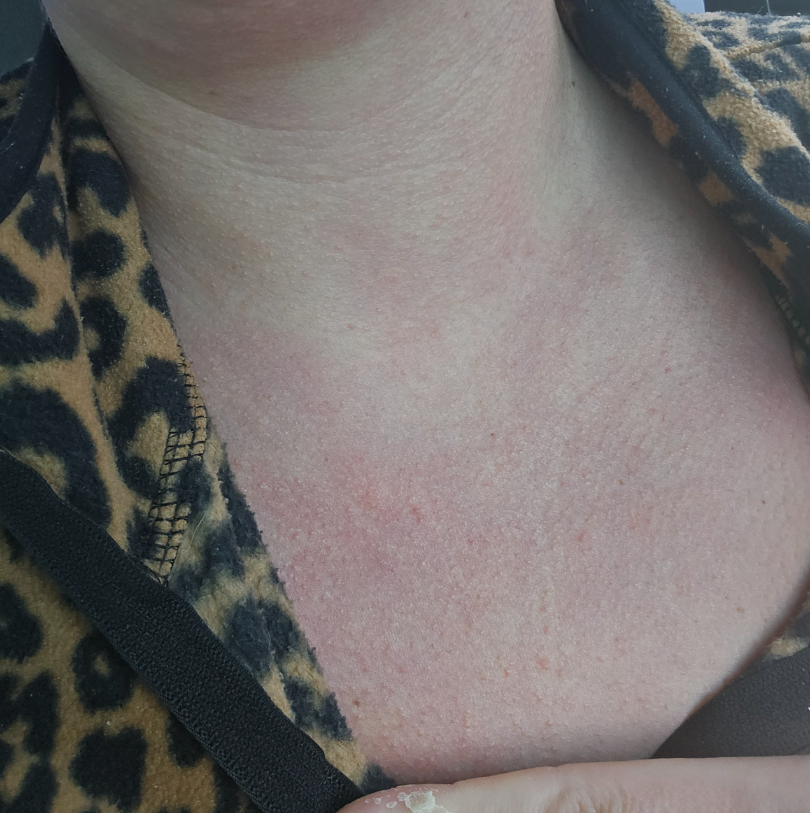The reviewing dermatologist was unable to assign a differential diagnosis from the image.